Fitzpatrick skin type II. A female subject roughly 80 years of age. A clinical photograph of a skin lesion — 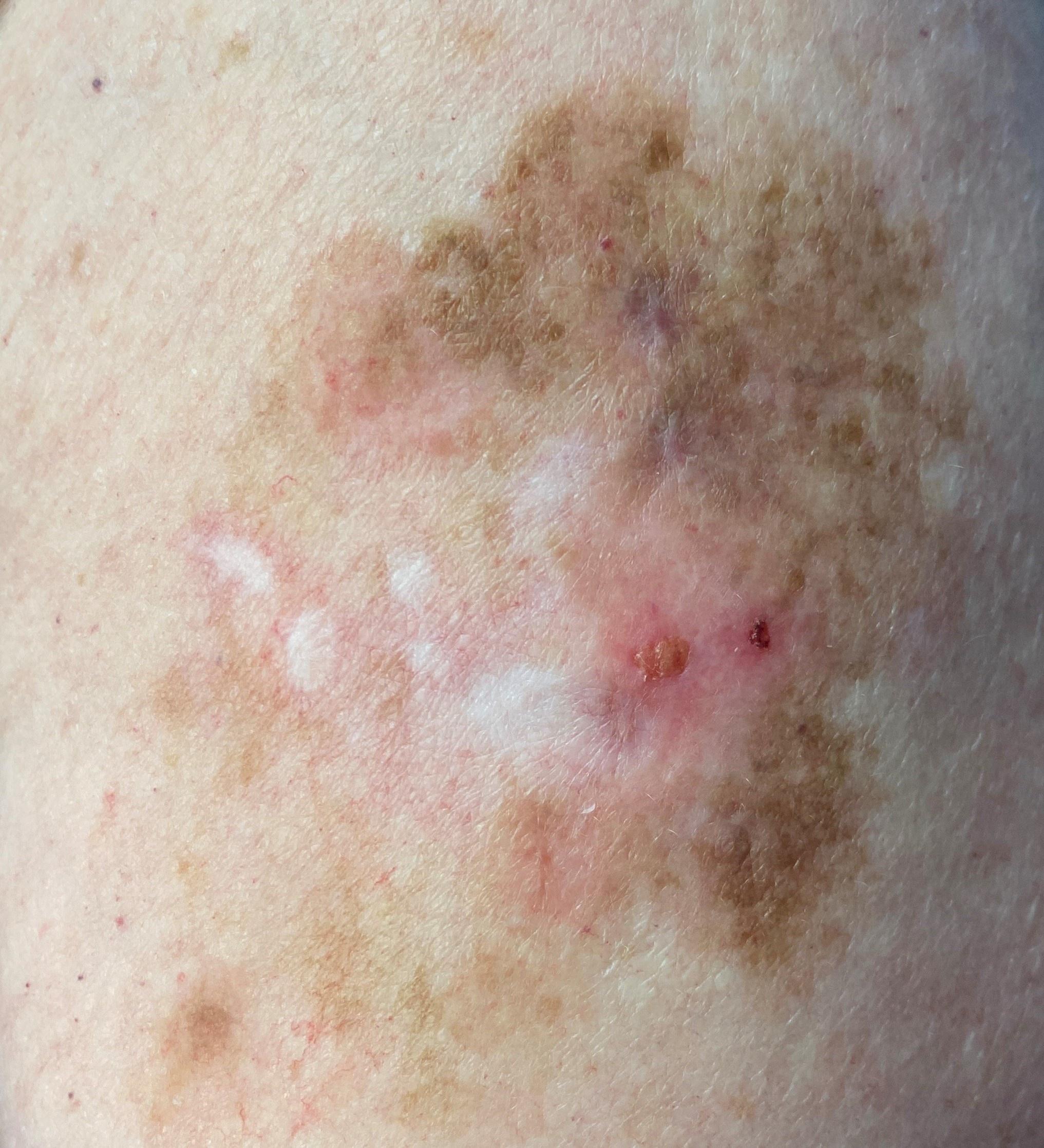anatomic site: an upper extremity; diagnostic label: Melanoma (biopsy-proven).